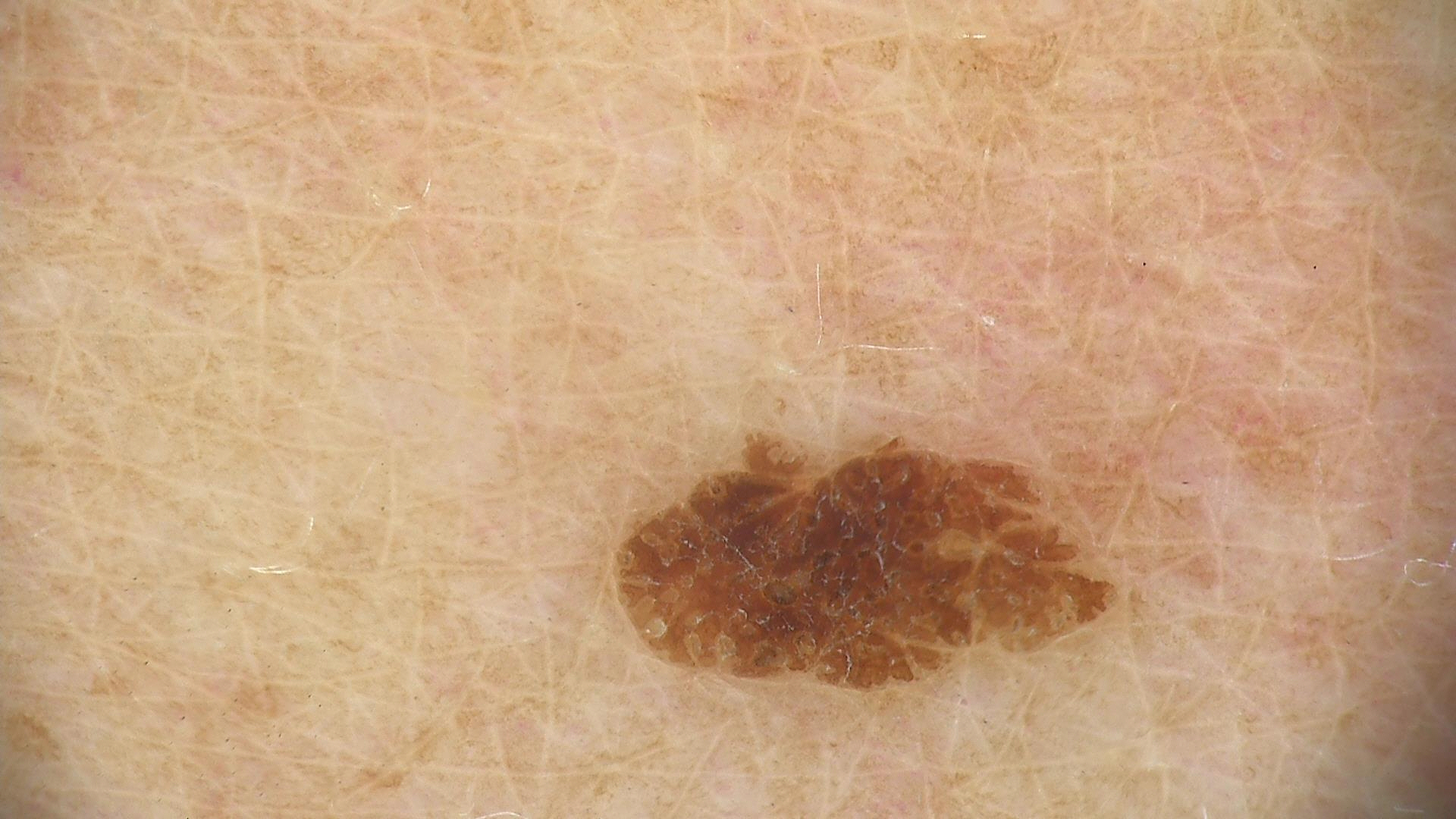{
  "image": "dermoscopy",
  "diagnosis": {
    "name": "seborrheic keratosis",
    "code": "sk",
    "malignancy": "benign",
    "super_class": "non-melanocytic",
    "confirmation": "expert consensus"
  }
}